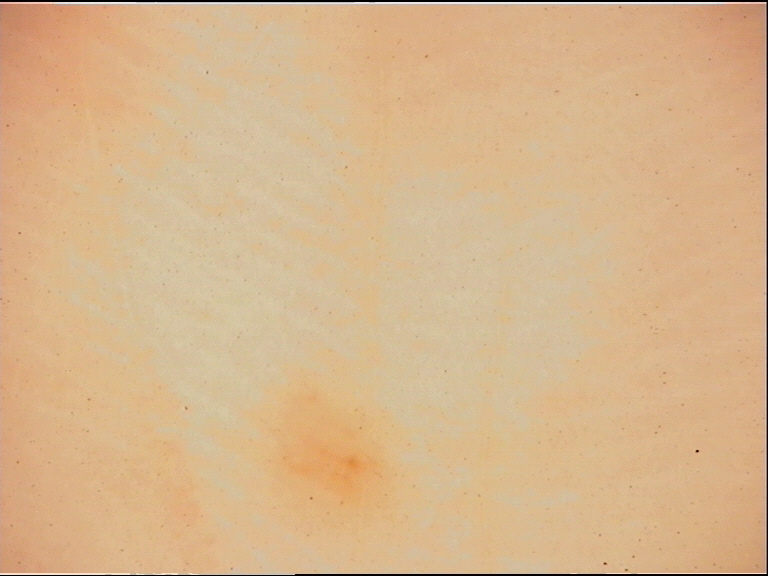A dermoscopic close-up of a skin lesion. The morphology is that of a banal lesion. The diagnosis was an acral junctional nevus.